Dermoscopy of a skin lesion.
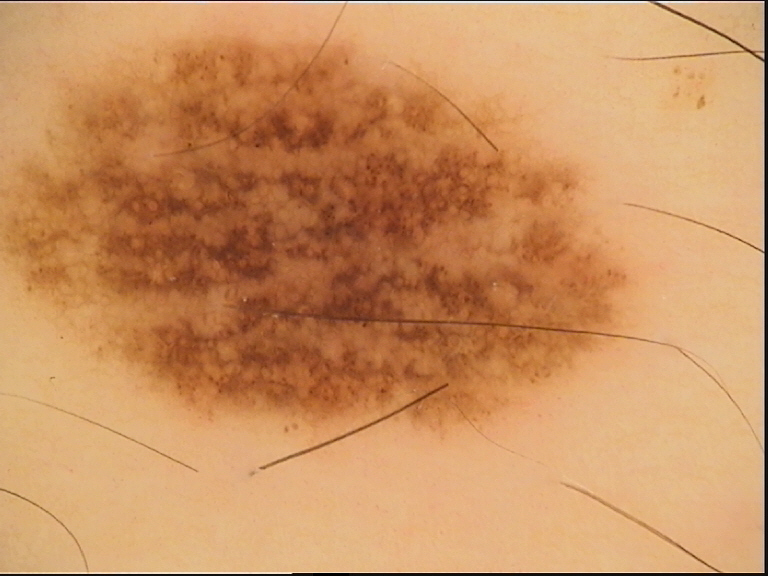Conclusion: Diagnosed as a benign lesion — a dysplastic compound nevus.